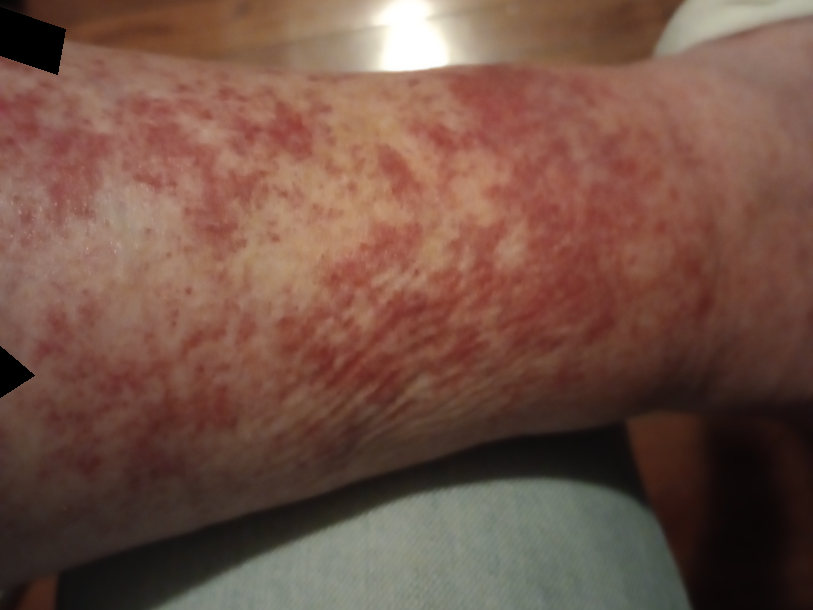Q: Could the case be diagnosed?
A: could not be assessed
Q: Where on the body?
A: leg
Q: Image view?
A: close-up
Q: Reported symptoms?
A: pain, bothersome appearance, burning and enlargement
Q: How does the patient describe it?
A: a rash
Q: Duration?
A: less than one week
Q: Texture?
A: raised or bumpy